Dermoscopy of a skin lesion.
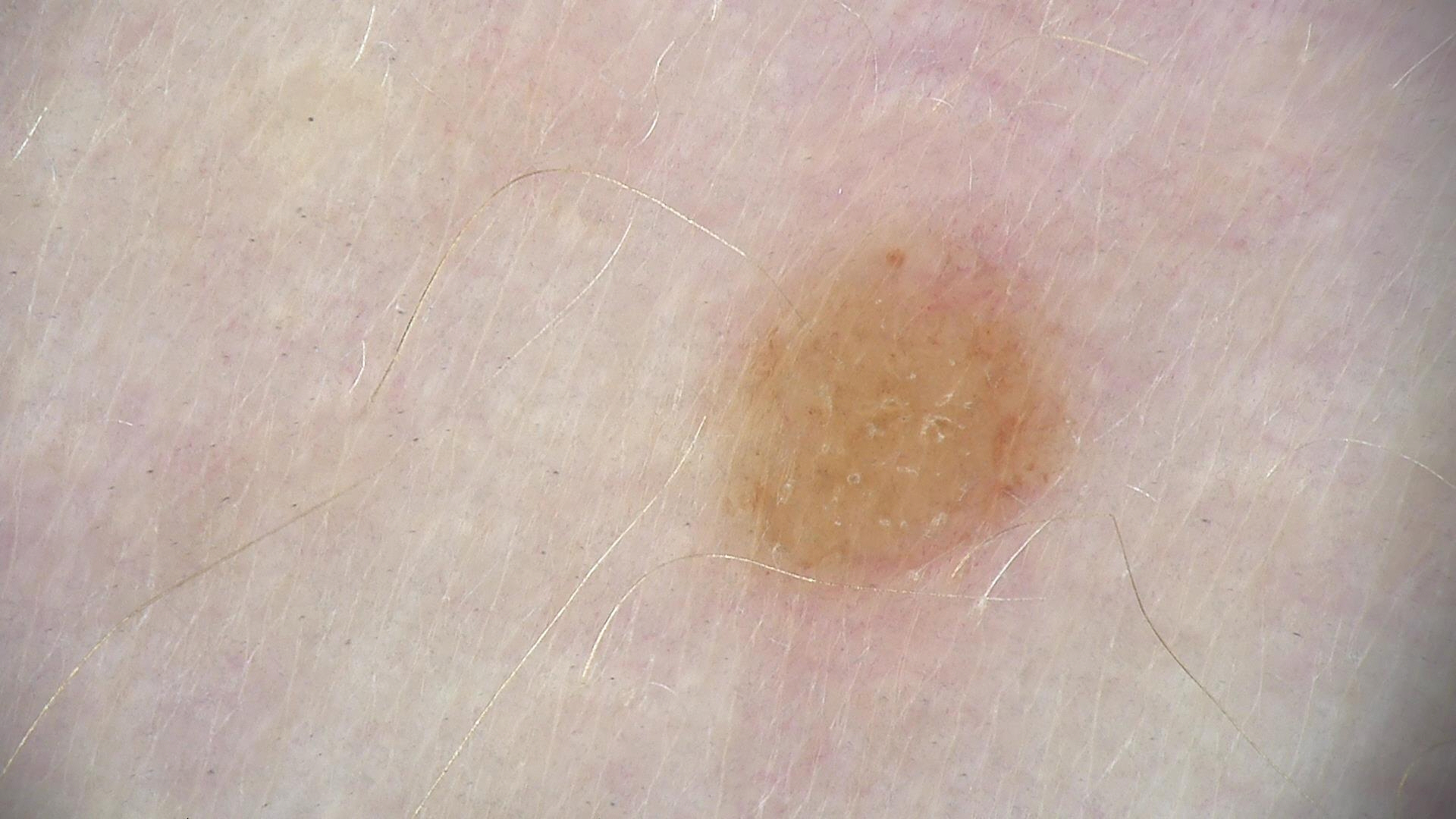Case:
The morphology is that of a banal lesion.
Conclusion:
The diagnosis was a dermal nevus.